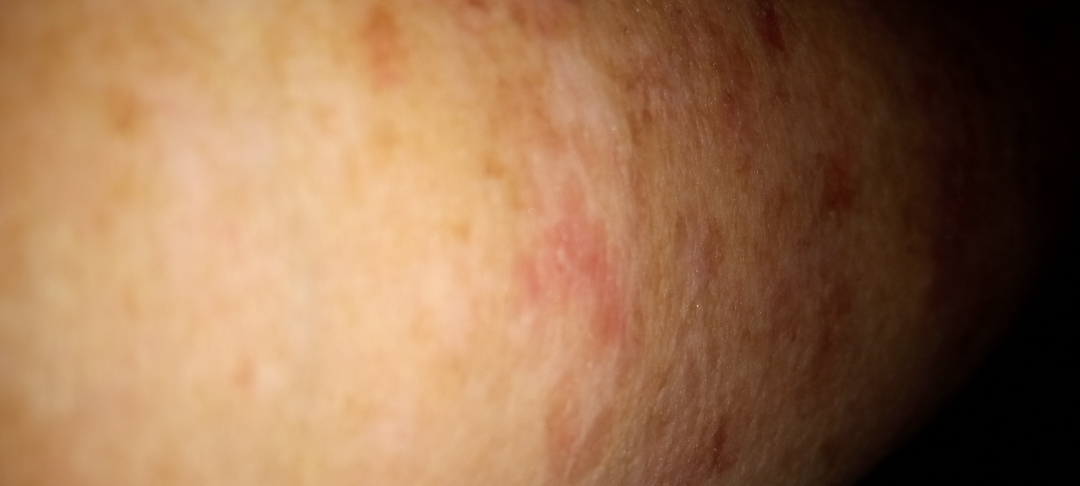| feature | finding |
|---|---|
| lesion symptoms | bleeding, bothersome appearance, darkening, itching, burning and enlargement |
| systemic symptoms | joint pain and fatigue |
| shot type | at an angle |
| site | arm and leg |
| patient | female, age 60–69 |
| lesion texture | rough or flaky and raised or bumpy |
| differential | Pigmented purpuric eruption and Stasis Dermatitis were considered with similar weight |